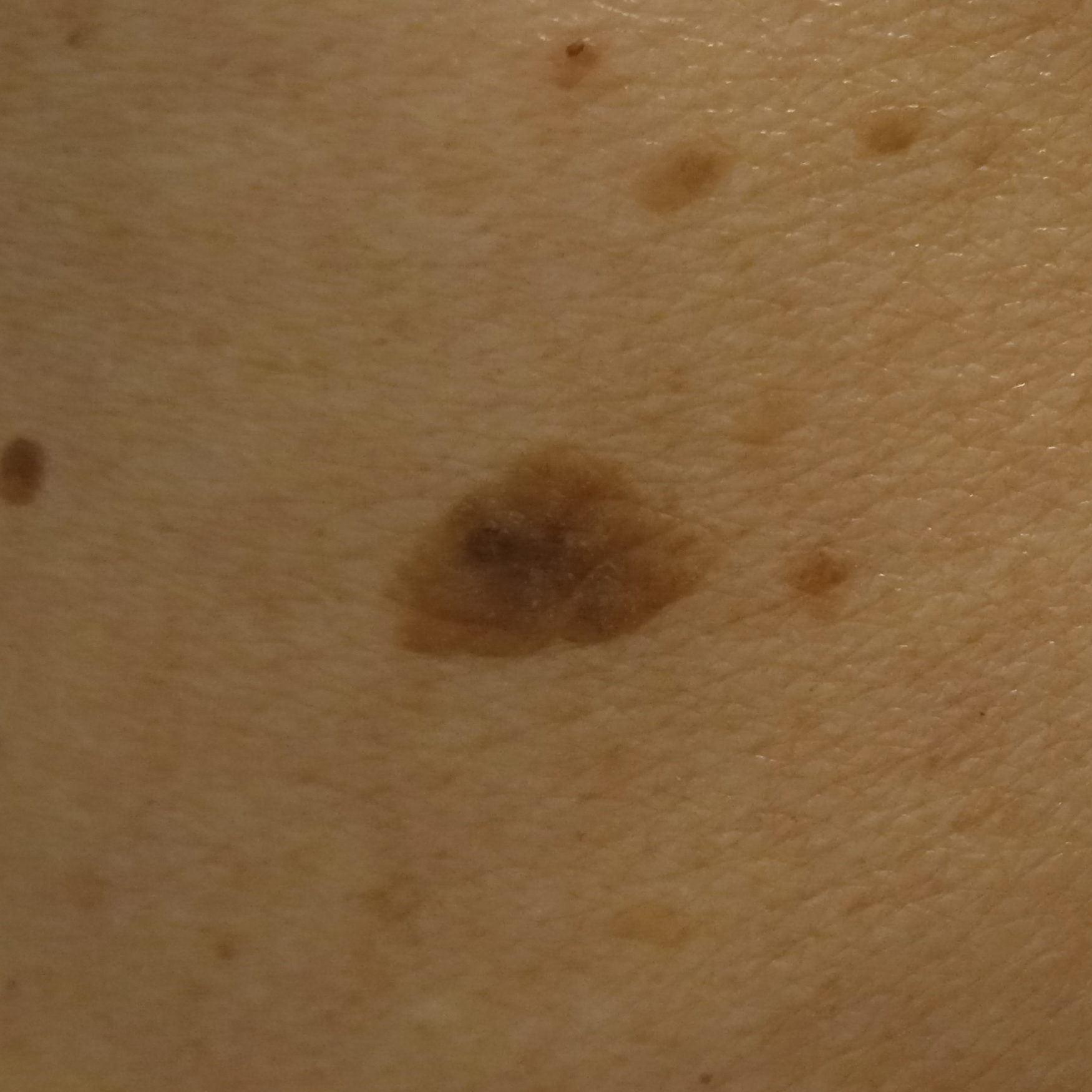Clinical context:
A moderate number of moles by the patient's own estimate. The patient says their skin reddens painfully with sun exposure. The patient reports immunosuppression, a personal history of cancer, and a personal history of skin cancer. A female subject 72 years of age. A clinical close-up of a skin lesion. The lesion is about 7.6 mm across.
Impression:
The consensus diagnosis for this lesion was a seborrheic keratosis.